The photograph was taken at a distance; the contributor is a female aged 40–49; the front of the torso, arm and head or neck are involved.
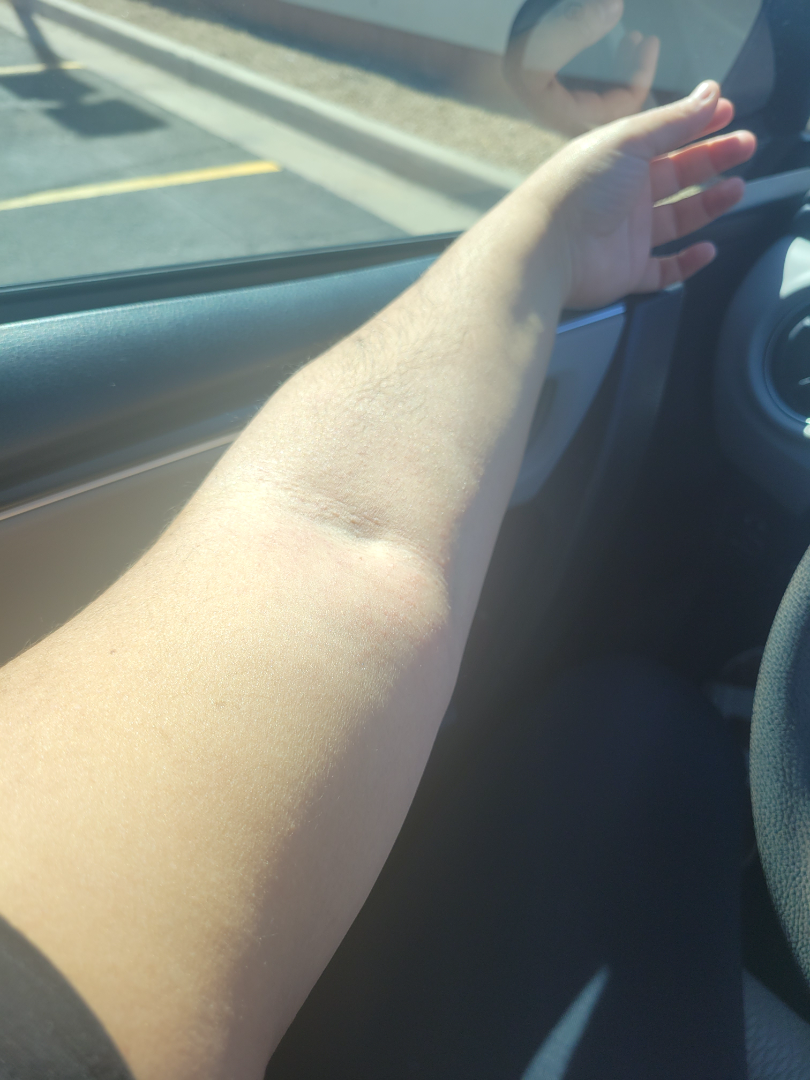Findings:
The dermatologist could not determine a likely condition from the photograph alone.